Dermoscopy of a skin lesion — 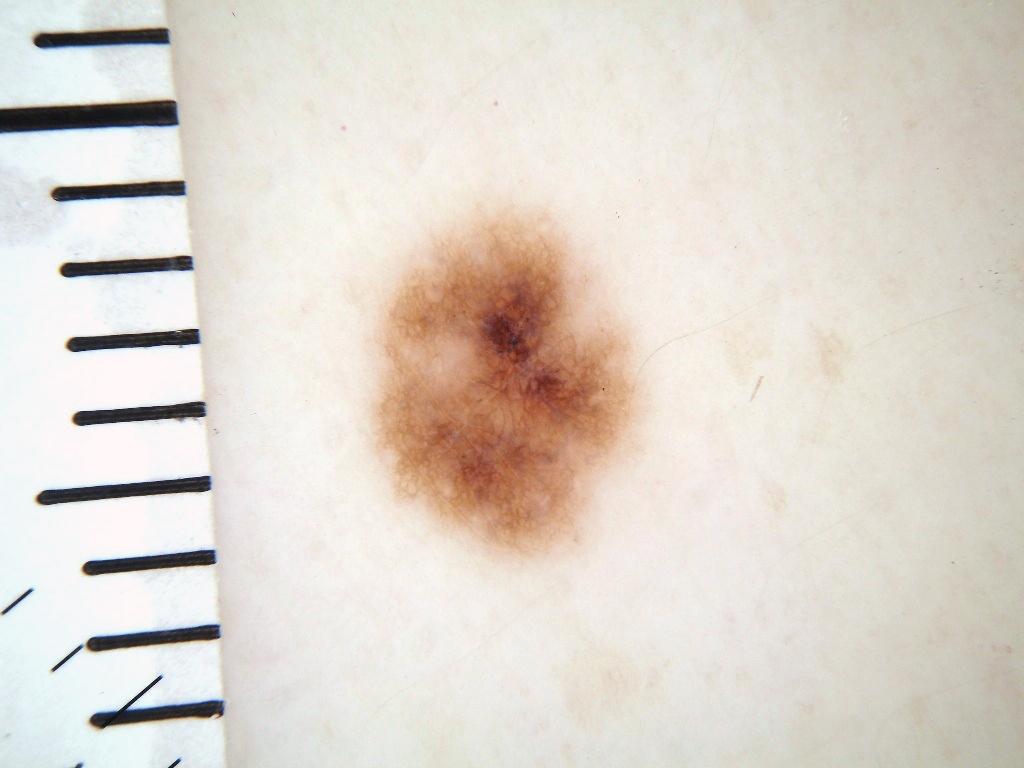With coordinates (x1, y1, x2, y2), the lesion is bounded by box(370, 208, 642, 561). The dermoscopic pattern shows globules, with no streaks. The clinical diagnosis was a benign lesion.